A dermoscopy image of a single skin lesion:
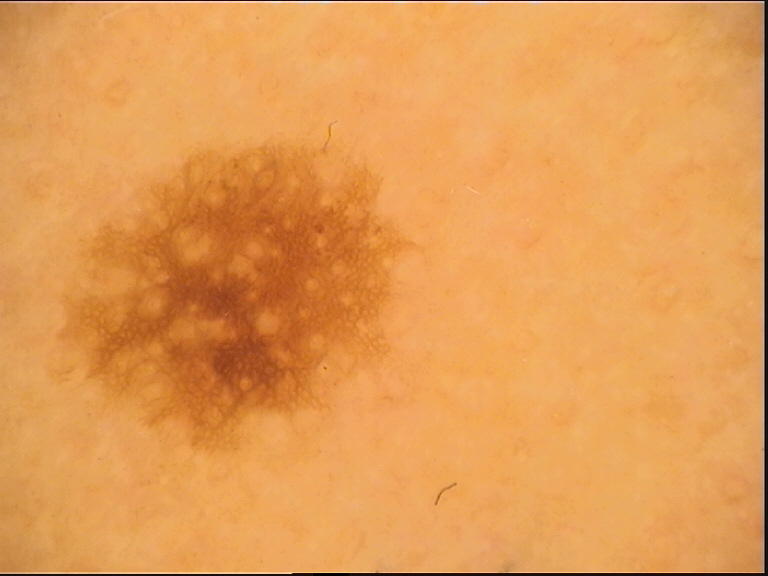  diagnosis:
    name: junctional nevus
    code: jb
    malignancy: benign
    super_class: melanocytic
    confirmation: expert consensus